A male subject about 70 years old; a clinical photograph showing a skin lesion in context: 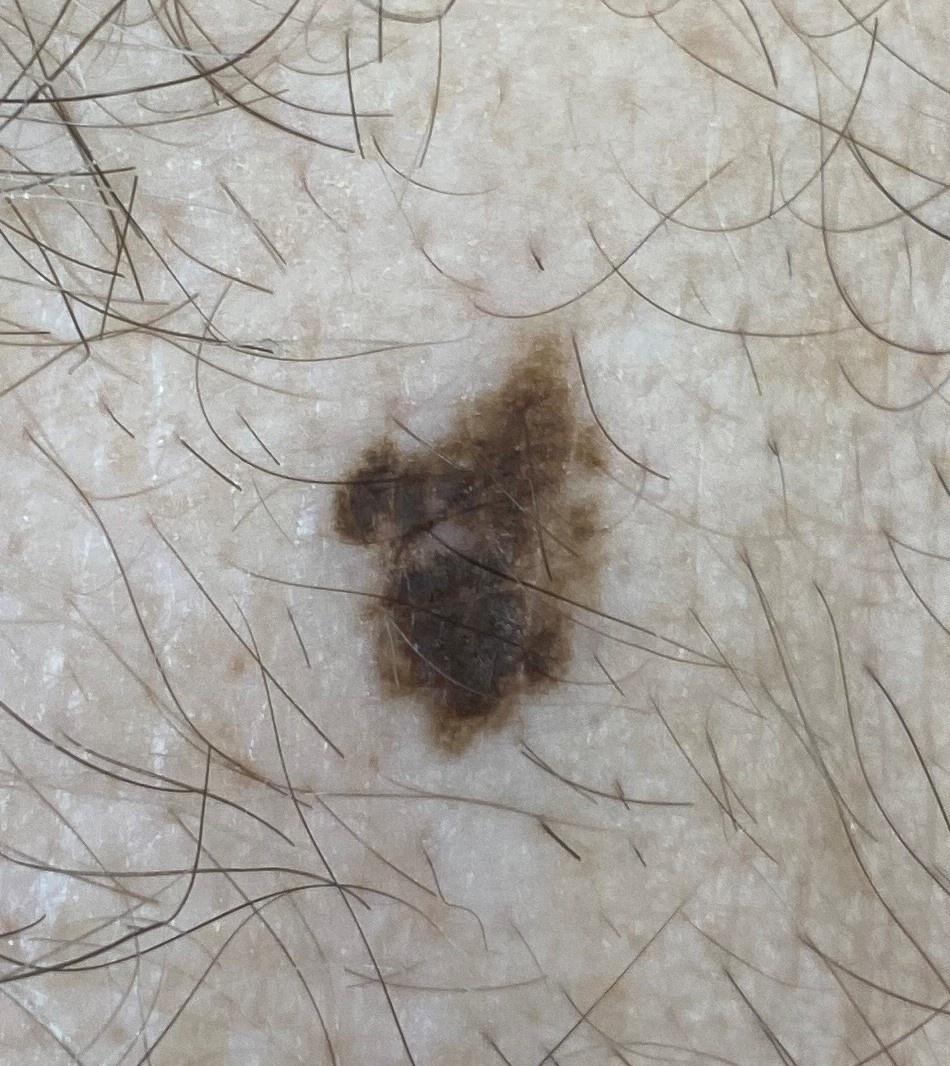Case:
• diagnosis: Melanoma (biopsy-proven)